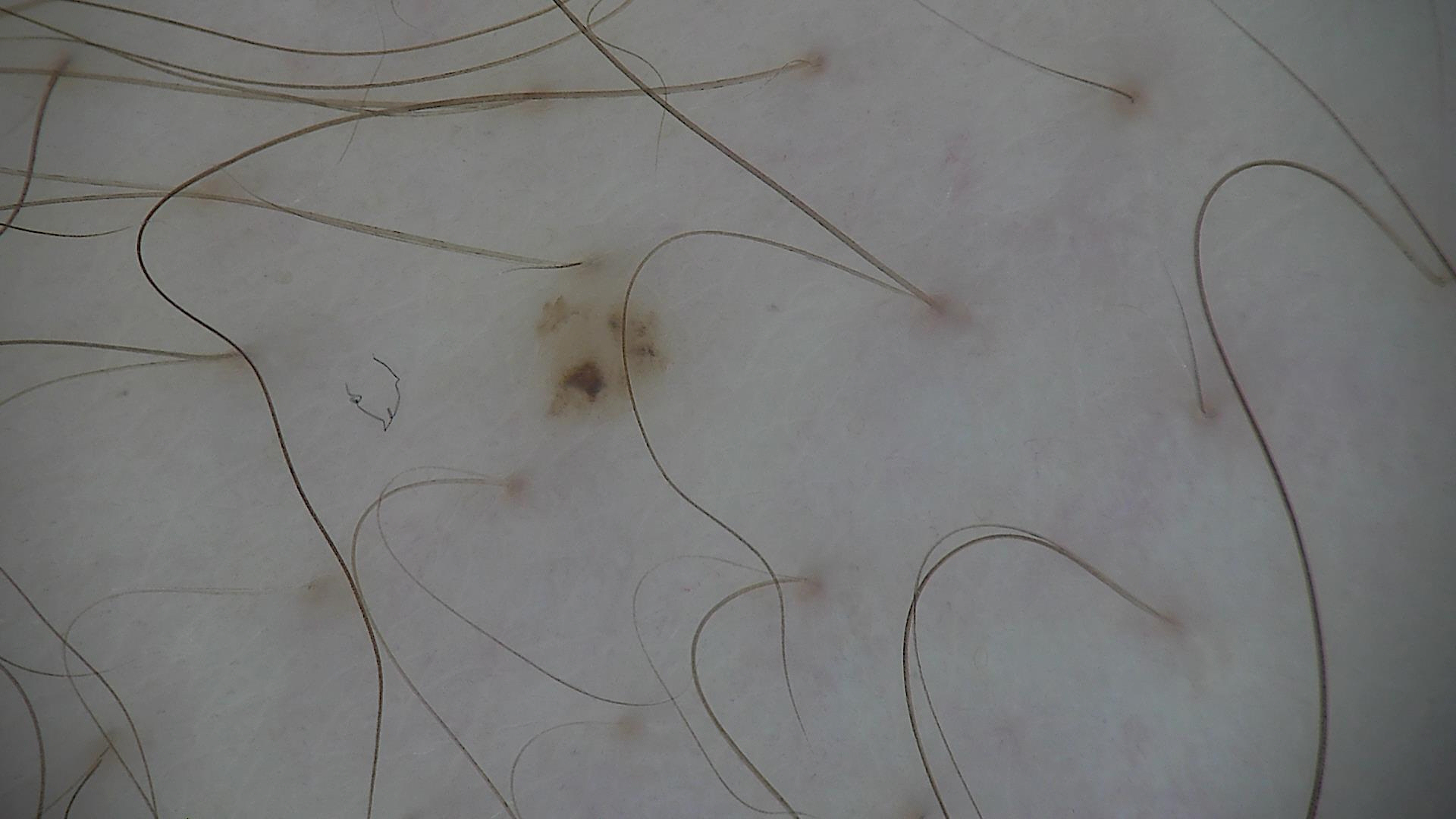A skin lesion imaged with a dermatoscope. Consistent with a dysplastic junctional nevus.